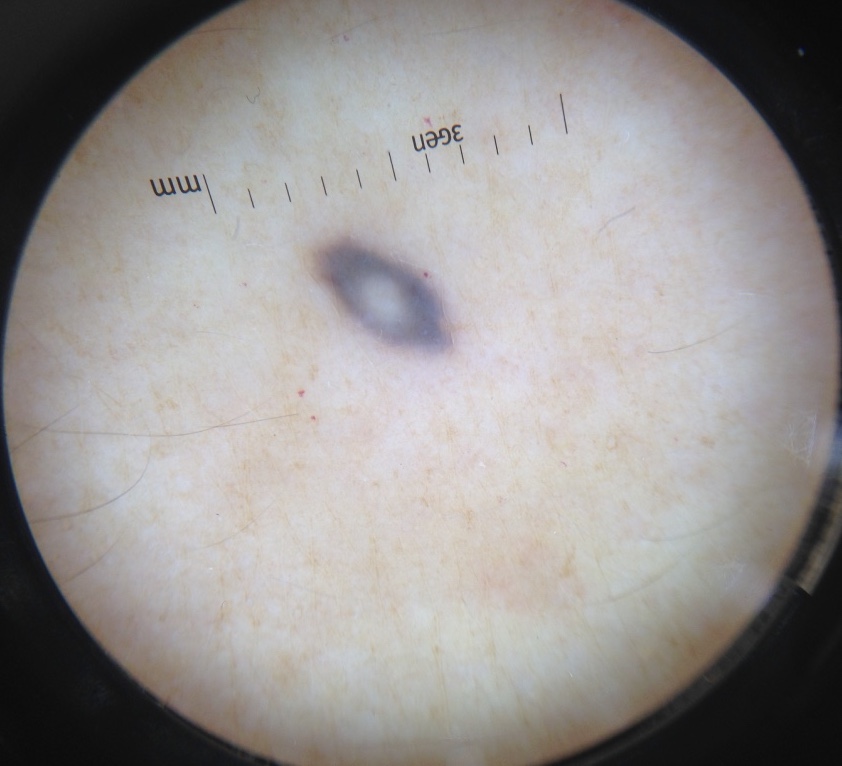Conclusion:
The diagnosis was a blue nevus.